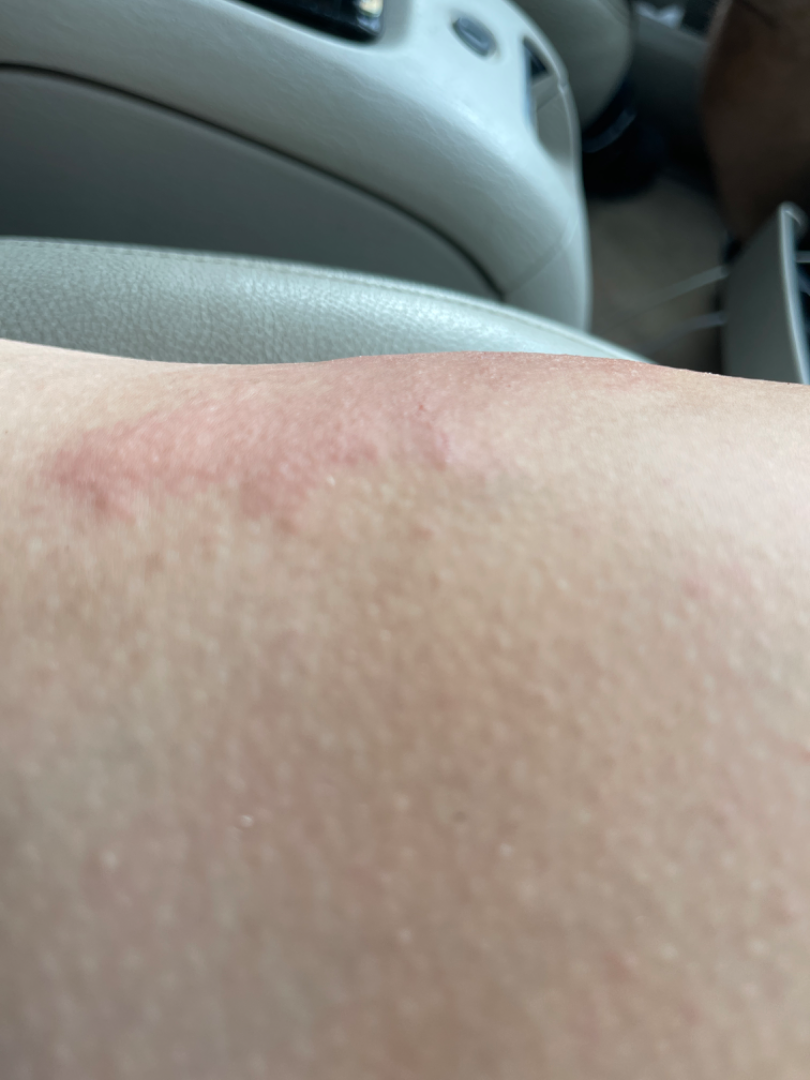The condition could not be reliably identified from the image.